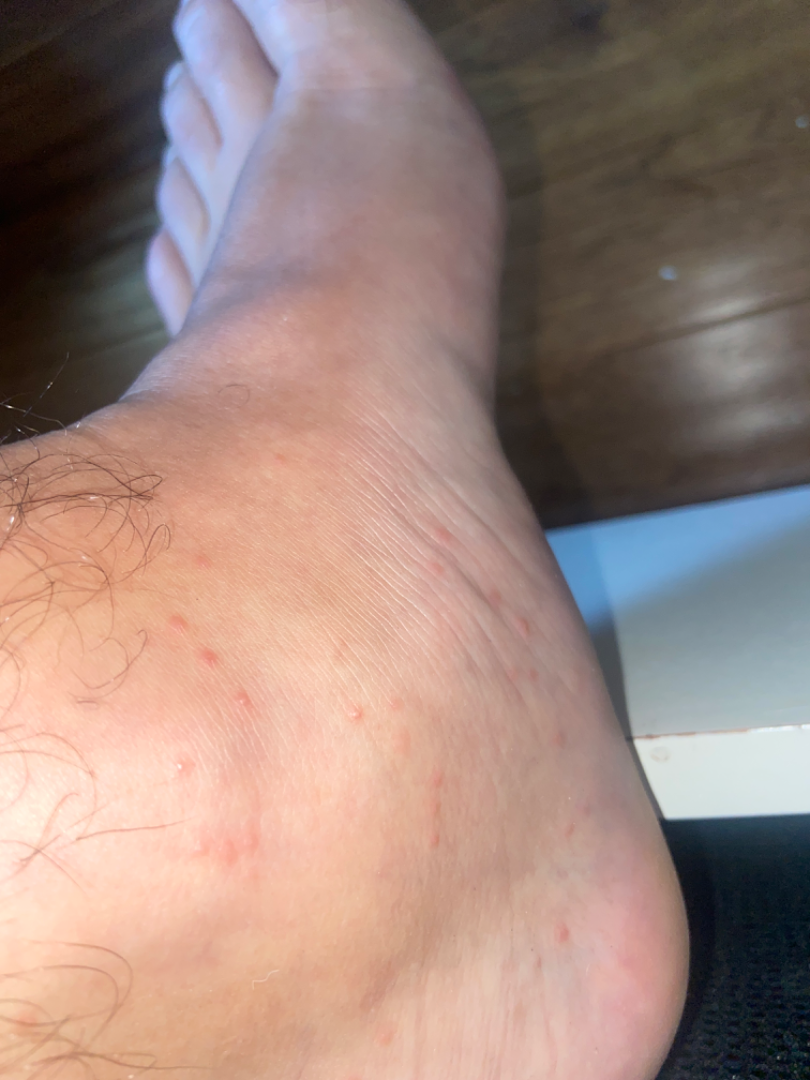The image was not sufficient for the reviewer to characterize the skin condition.
The photograph was taken at an angle.
The lesion involves the top or side of the foot.